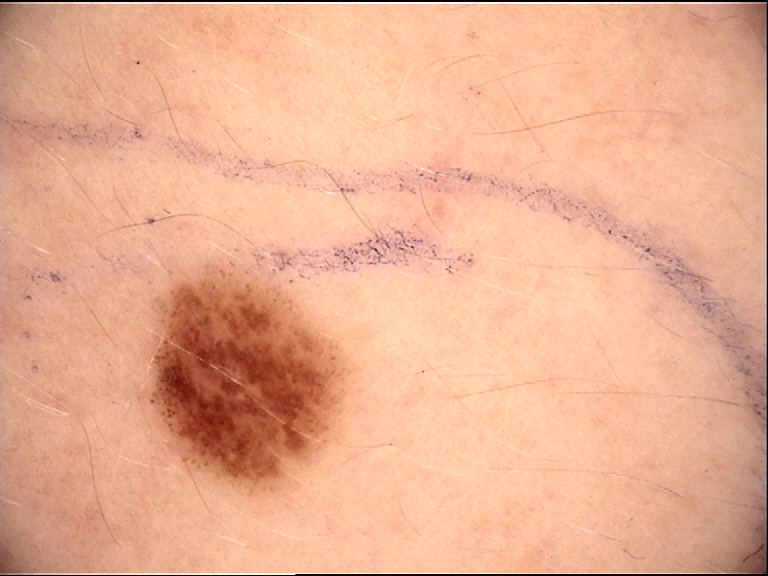A dermoscopic image of a skin lesion. Diagnosed as a benign lesion — a dysplastic junctional nevus.